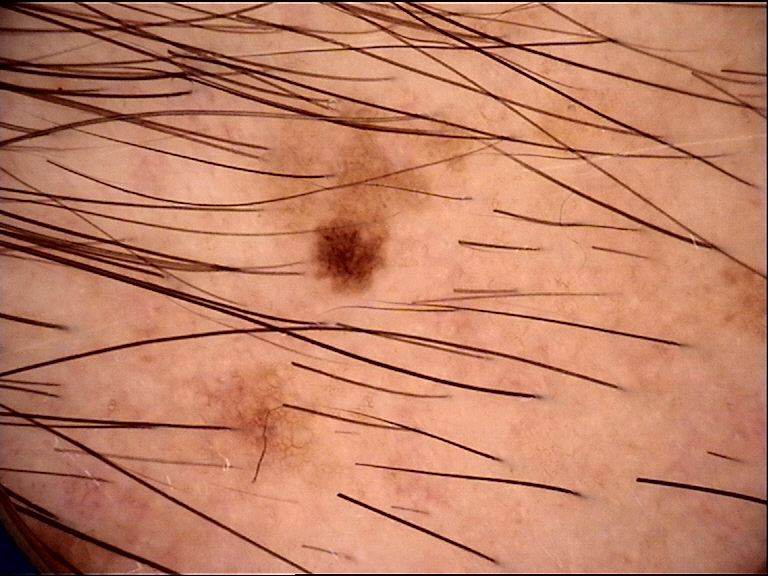diagnosis: dysplastic junctional nevus (expert consensus)